The contributor is male. The photo was captured at an angle. The lesion involves the front of the torso, top or side of the foot, back of the hand, arm, head or neck and back of the torso — 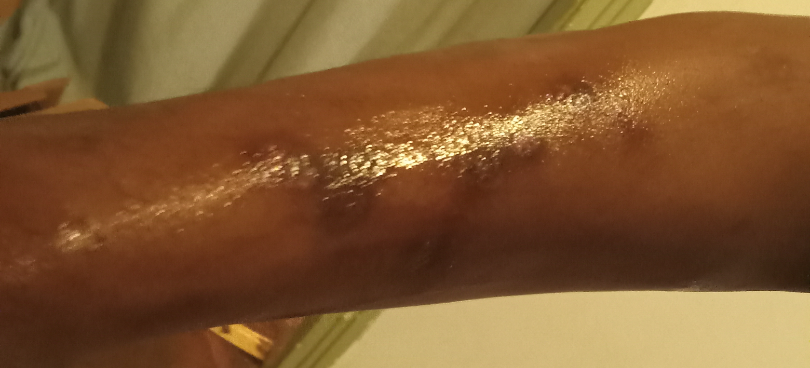The case was indeterminate on photographic review.